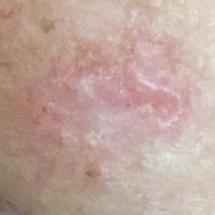Fitzpatrick: II | subject: female, aged 62 | modality: smartphone clinical photo | location: the nose | symptoms: growth, itching, pain, bleeding | diagnostic label: basal cell carcinoma (biopsy-proven).